A dermoscopic close-up of a skin lesion.
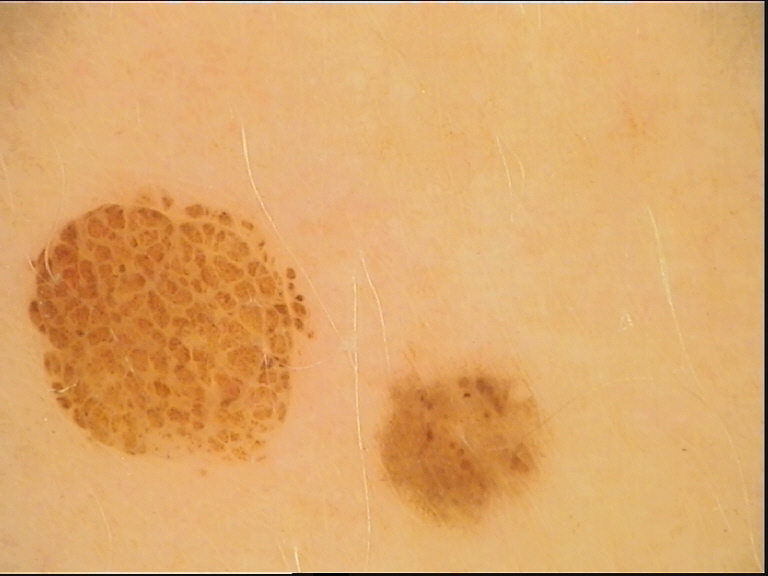Conclusion:
Classified as a dysplastic compound nevus.